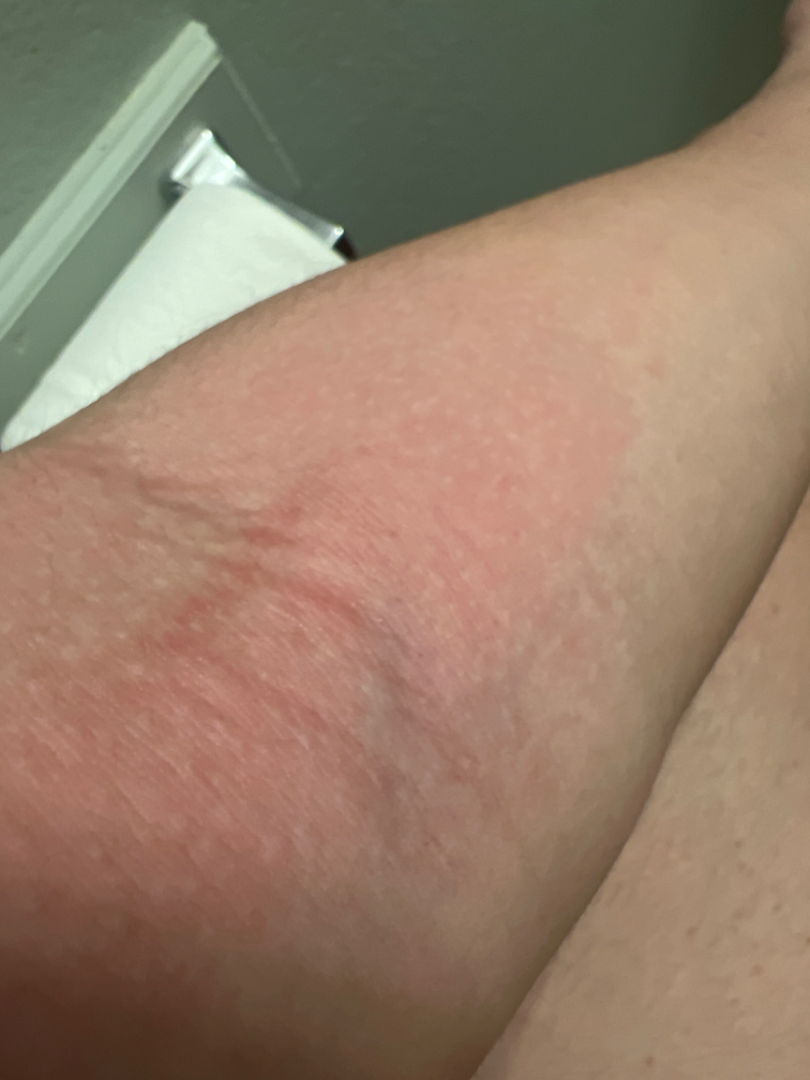Eczema (favored); Urticaria (possible); Irritant Contact Dermatitis (possible); Acute dermatitis, NOS (unlikely); Allergic Contact Dermatitis (unlikely); Cellulitis (unlikely).